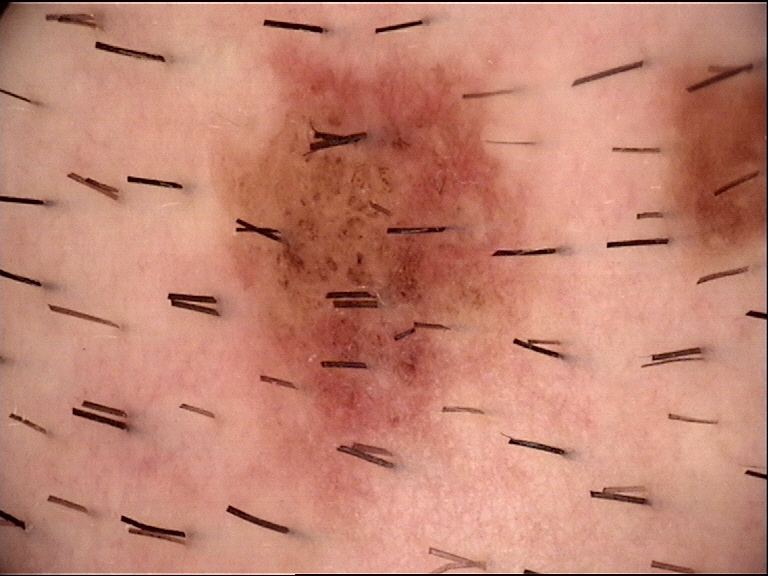Summary: A dermoscopy image of a single skin lesion. Conclusion: Diagnosed as a dysplastic compound nevus.